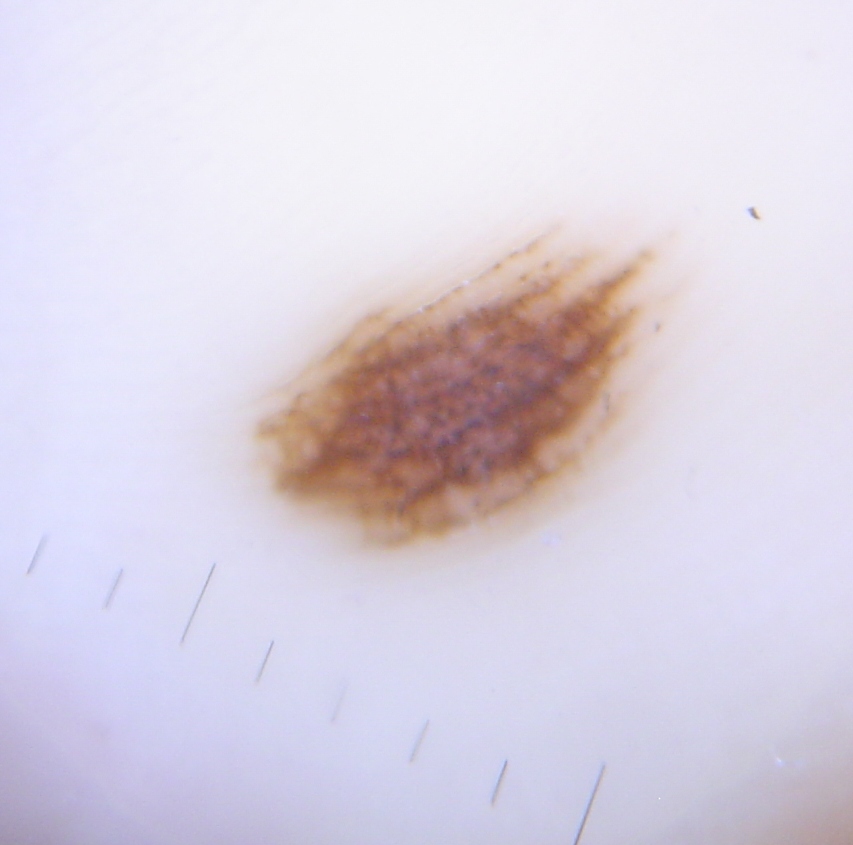Summary:
A dermoscopy image of a single skin lesion.
Conclusion:
Labeled as an acral dysplastic junctional nevus.